A dermoscopic photograph of a skin lesion:
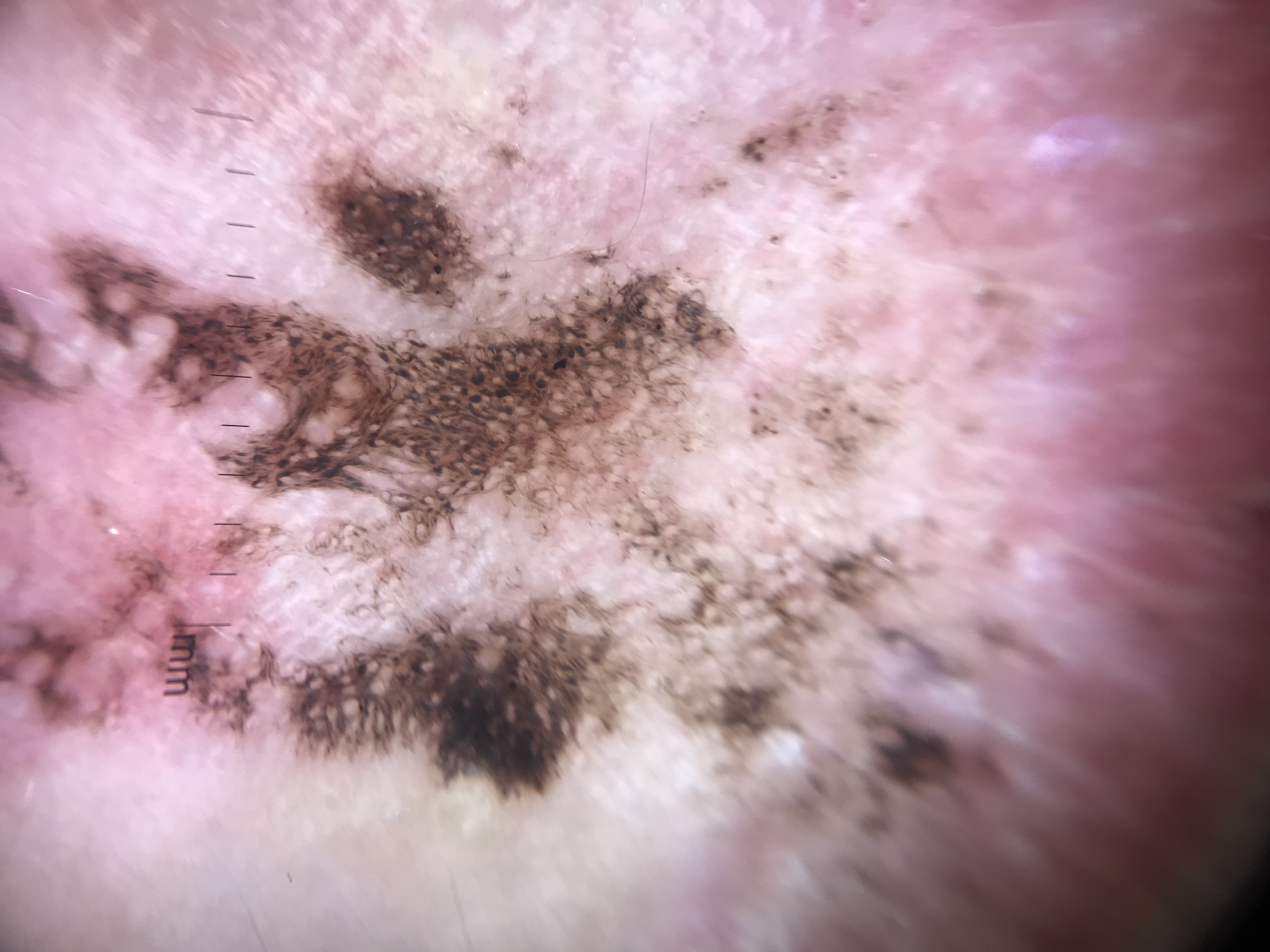Findings:
* pathology — melanoma (biopsy-proven)